A male patient aged 33 to 37, dermoscopy of a skin lesion: 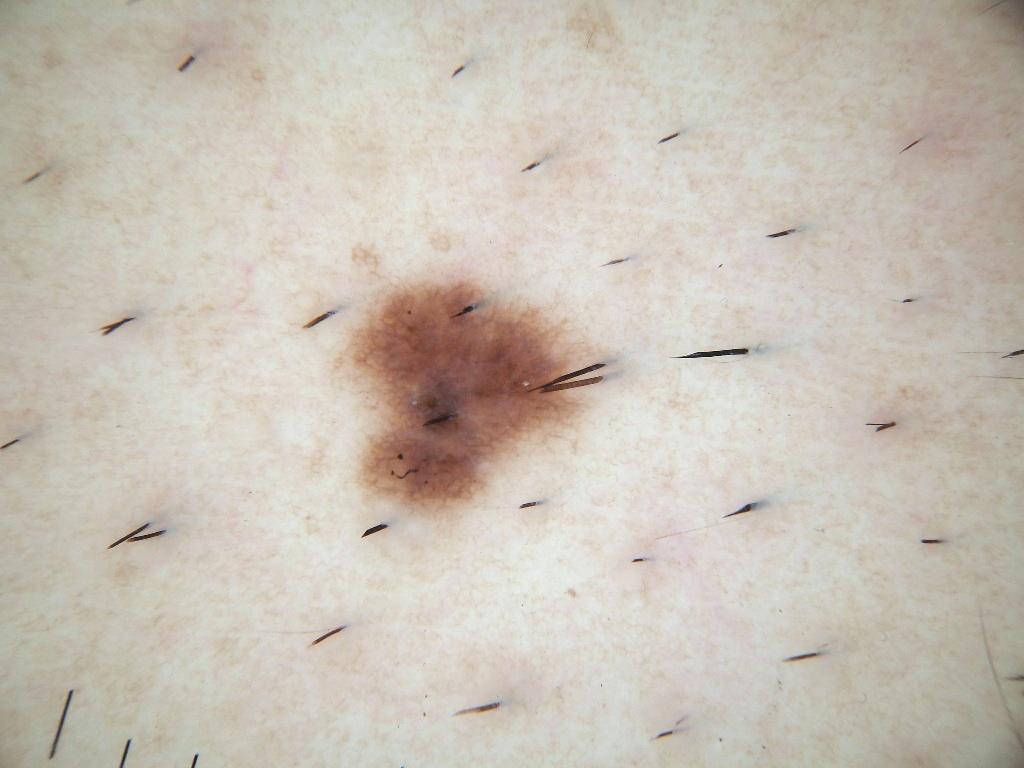Summary: As (left, top, right, bottom), the lesion's extent is (341, 274, 608, 518). Dermoscopic review identifies pigment network, with no negative network, globules, streaks, or milia-like cysts. The lesion covers approximately 5% of the dermoscopic field. Conclusion: Diagnosed as a melanocytic nevus, a benign skin lesion.